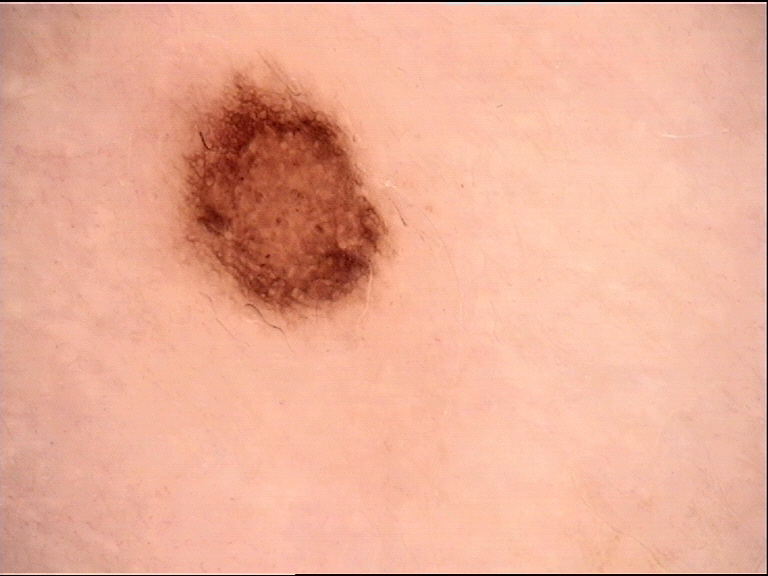A dermoscopy image of a single skin lesion.
Diagnosed as a benign lesion — a dysplastic junctional nevus.